A female subject 81 years of age. Imaged for a research study, with no referral diagnosis recorded. A moderate number of moles by the patient's own estimate. The patient says their skin reddens painfully with sun exposure. The patient reports no sunbed use and no personal history of cancer.
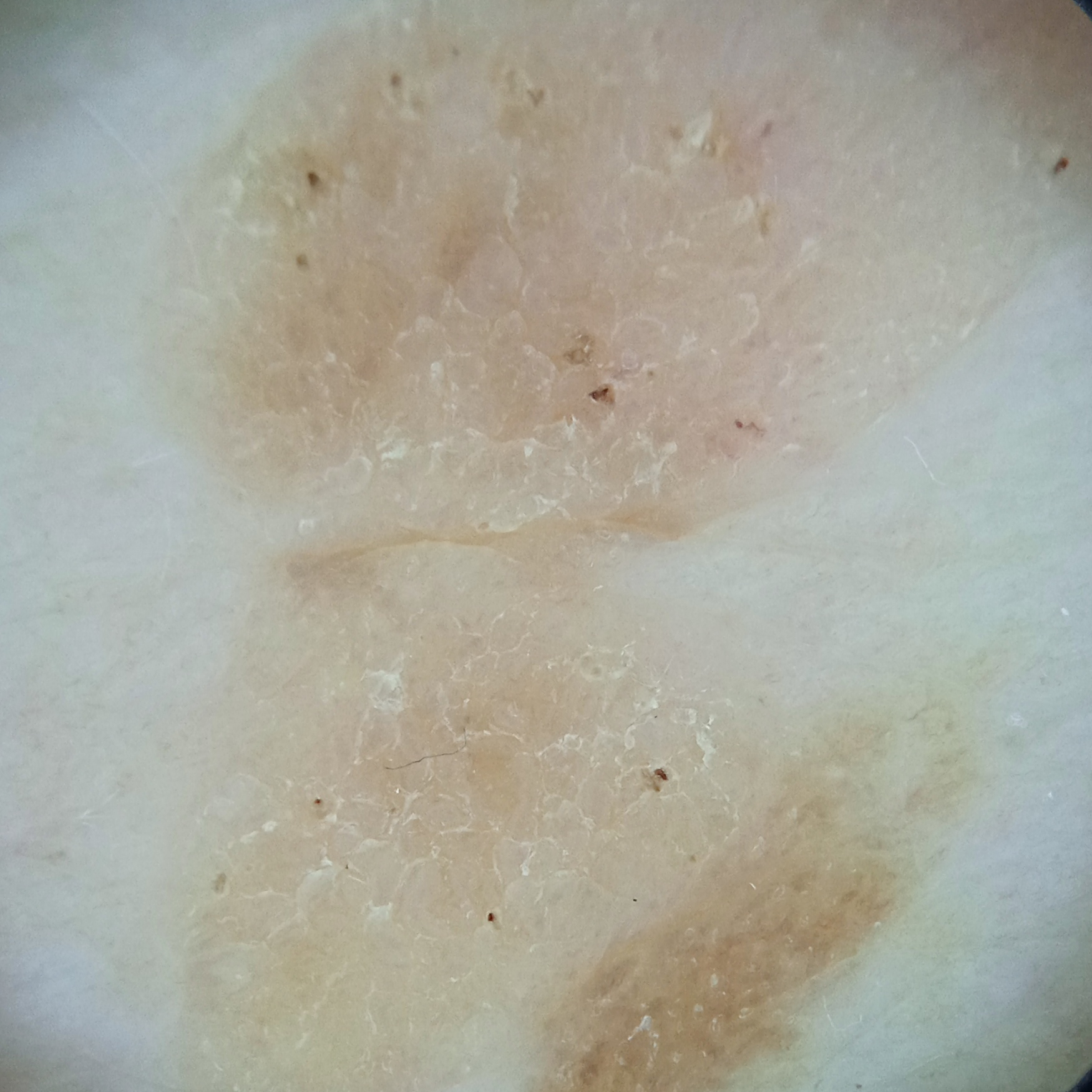Findings:
• size · 15.5 mm
• assessment · seborrheic keratosis (dermatologist consensus)